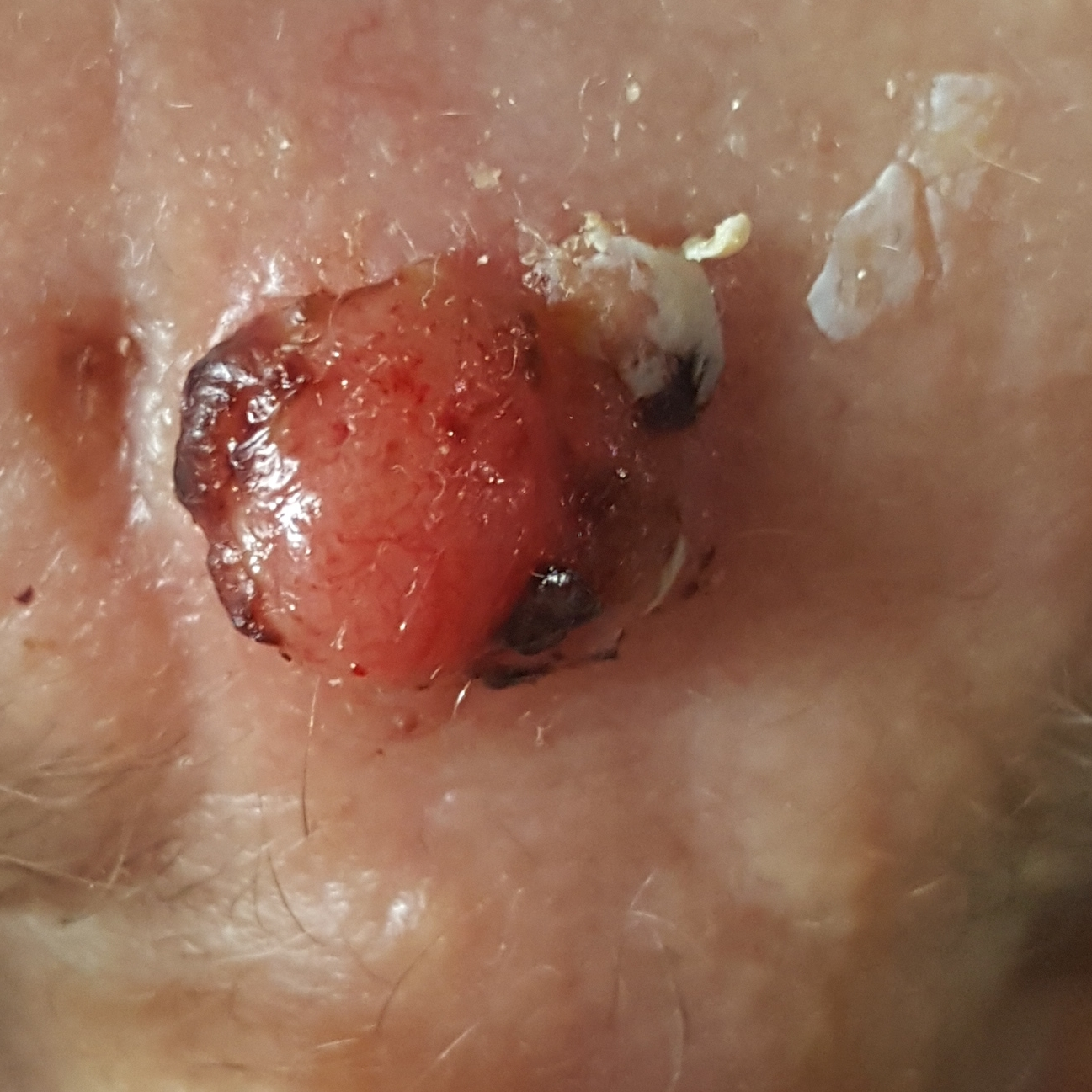Q: How was this image acquired?
A: clinical photo
Q: Patient demographics?
A: female, aged 91
Q: What is the anatomic site?
A: the face
Q: What symptoms does the patient report?
A: growth, bleeding, elevation, itching, change in appearance
Q: What did the workup show?
A: squamous cell carcinoma (biopsy-proven)